A male patient about 45 years old; a clinical photograph showing a skin lesion in context; FST II.
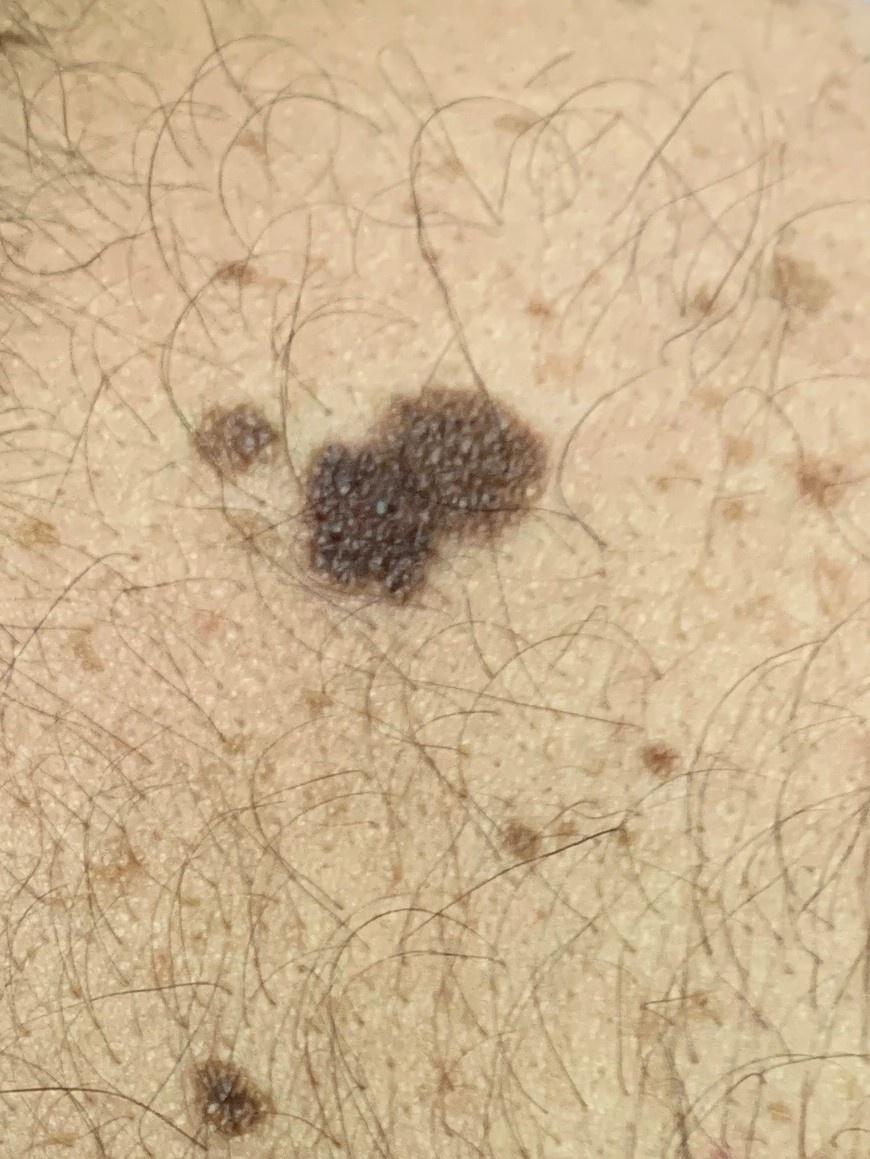diagnostic label = Nevus (biopsy-proven)